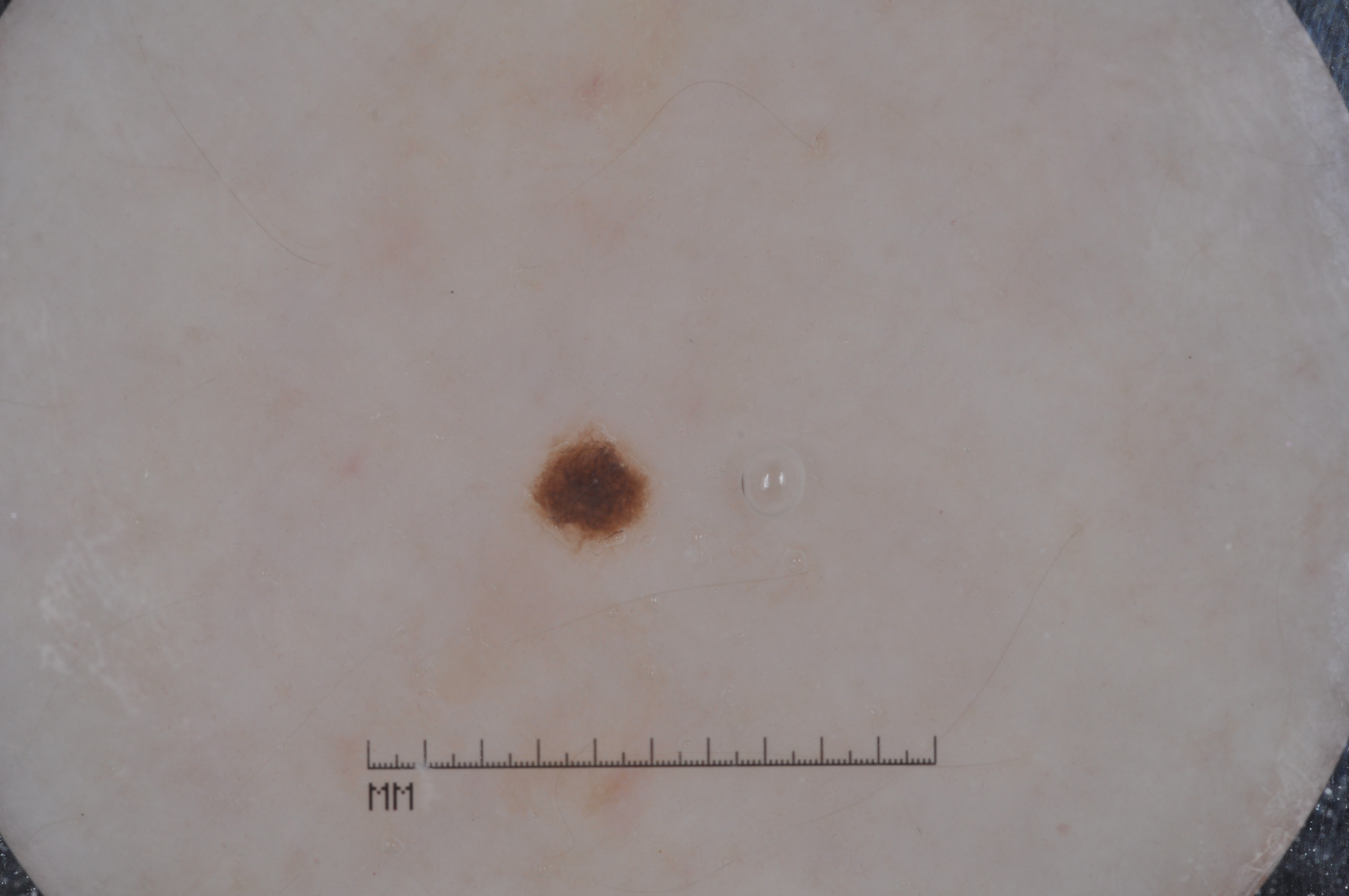{"image": {"modality": "dermoscopy"}, "patient": {"sex": "female", "age_approx": 80}, "lesion_extent": {"approx_field_fraction_pct": 1}, "dermoscopic_features": {"present": ["pigment network", "milia-like cysts"], "absent": ["negative network", "streaks"]}, "lesion_location": {"bbox_xyxy": [538, 434, 643, 539]}, "diagnosis": {"name": "melanocytic nevus", "malignancy": "benign", "lineage": "melanocytic", "provenance": "clinical"}}